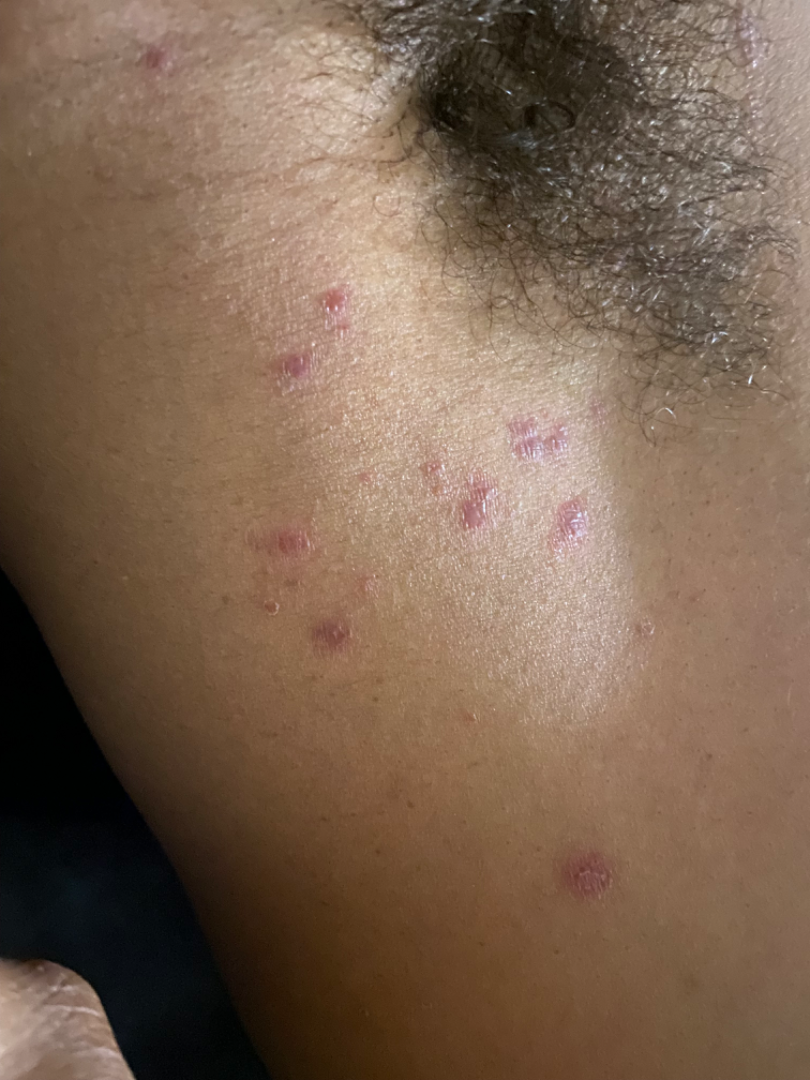Findings:
• shot type: at a distance
• skin tone: FST III; lay reviewers estimated Monk Skin Tone 3–4
• dermatologist impression: most consistent with Lichen planus/lichenoid eruption